The photo was captured at an angle. The arm is involved. Present for less than one week. No relevant systemic symptoms. Skin tone: Fitzpatrick III. The lesion is described as rough or flaky. The patient described the issue as a rash. Symptoms reported: itching and enlargement.
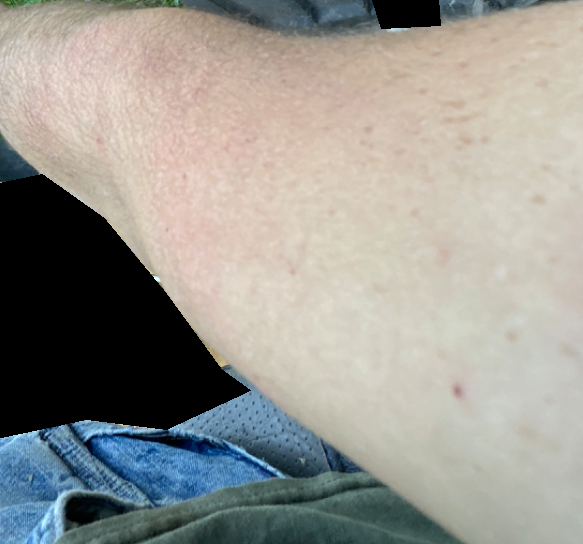diagnostic considerations = the differential, in no particular order, includes Eczema, Allergic Contact Dermatitis and Irritant Contact Dermatitis.